Dermoscopy of a skin lesion.
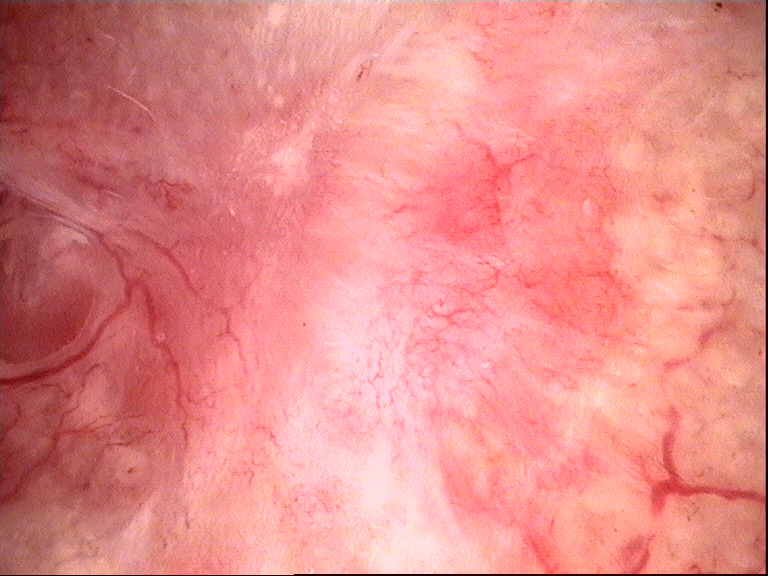<case>
<diagnosis>
<name>basal cell carcinoma</name>
<code>bcc</code>
<malignancy>malignant</malignancy>
<super_class>non-melanocytic</super_class>
<confirmation>histopathology</confirmation>
</diagnosis>
</case>